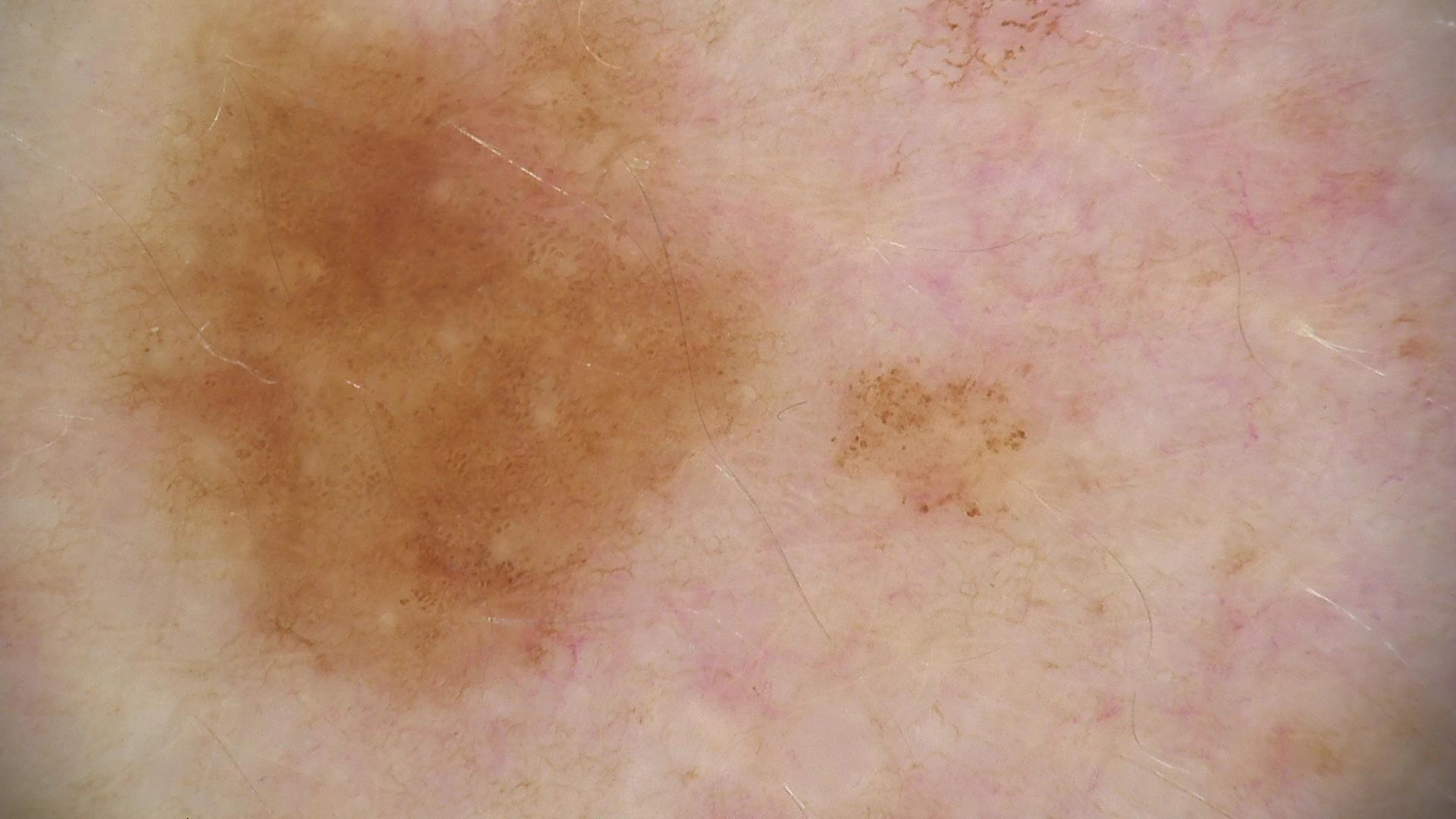Dermoscopy of a skin lesion.
The diagnostic label was a benign lesion — a dysplastic junctional nevus.